The patient is a female in their mid- to late 80s or older. A skin lesion imaged with a dermatoscope.
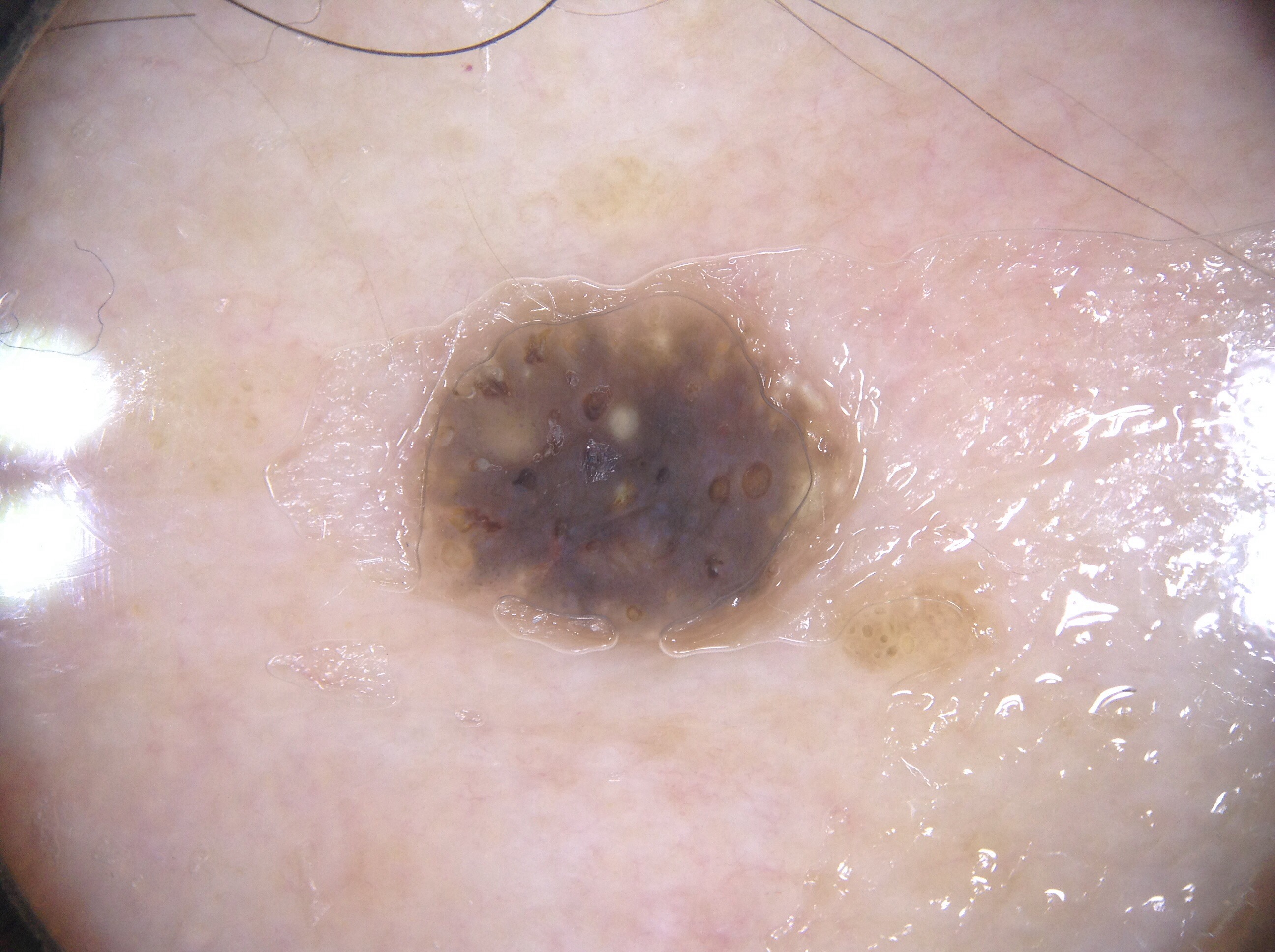Summary:
In (x1, y1, x2, y2) order, the lesion is located at bbox(409, 290, 847, 647). The lesion takes up a moderate portion of the field. Dermoscopic assessment notes milia-like cysts, with no pigment network, streaks, or negative network.
Assessment:
Diagnosed as a seborrheic keratosis, a lesion of keratinocytic origin.